The patient reported no systemic symptoms. This image was taken at a distance. The contributor is a male aged 30–39. The patient indicates itching. Texture is reported as raised or bumpy. The patient indicates the condition has been present for less than one week: 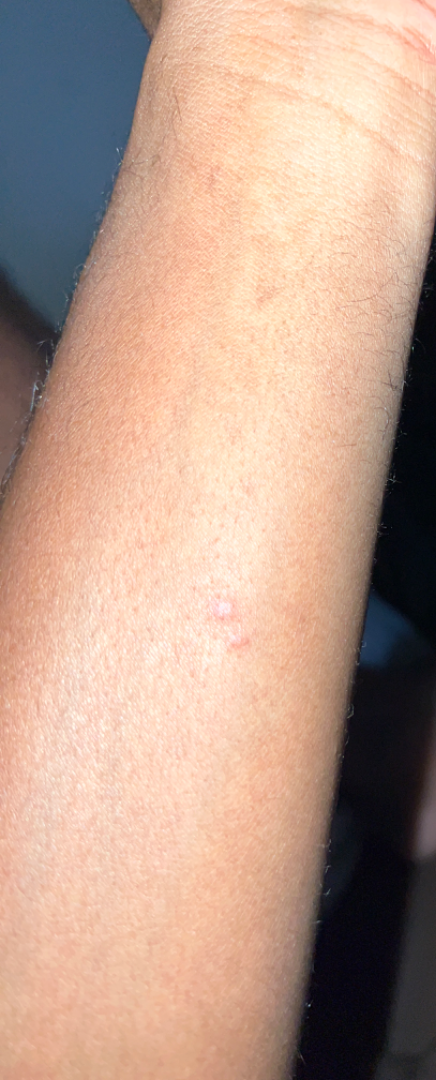Q: What is the dermatologist's impression?
A: Insect Bite (weight 0.67); Allergic Contact Dermatitis (weight 0.33)